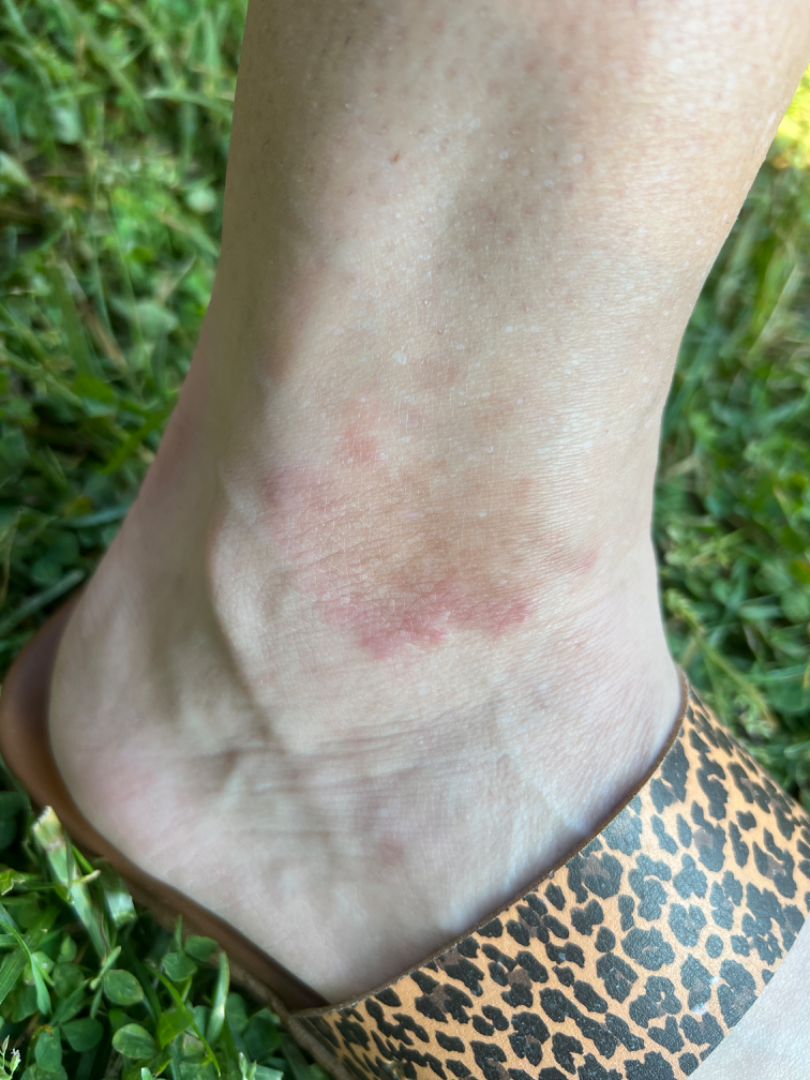Present for more than one year. Self-categorized by the patient as a rash. Female patient, age 30–39. No relevant systemic symptoms. The affected area is the top or side of the foot. The photograph is a close-up of the affected area. On photographic review by a dermatologist, Granuloma annulare (most likely).